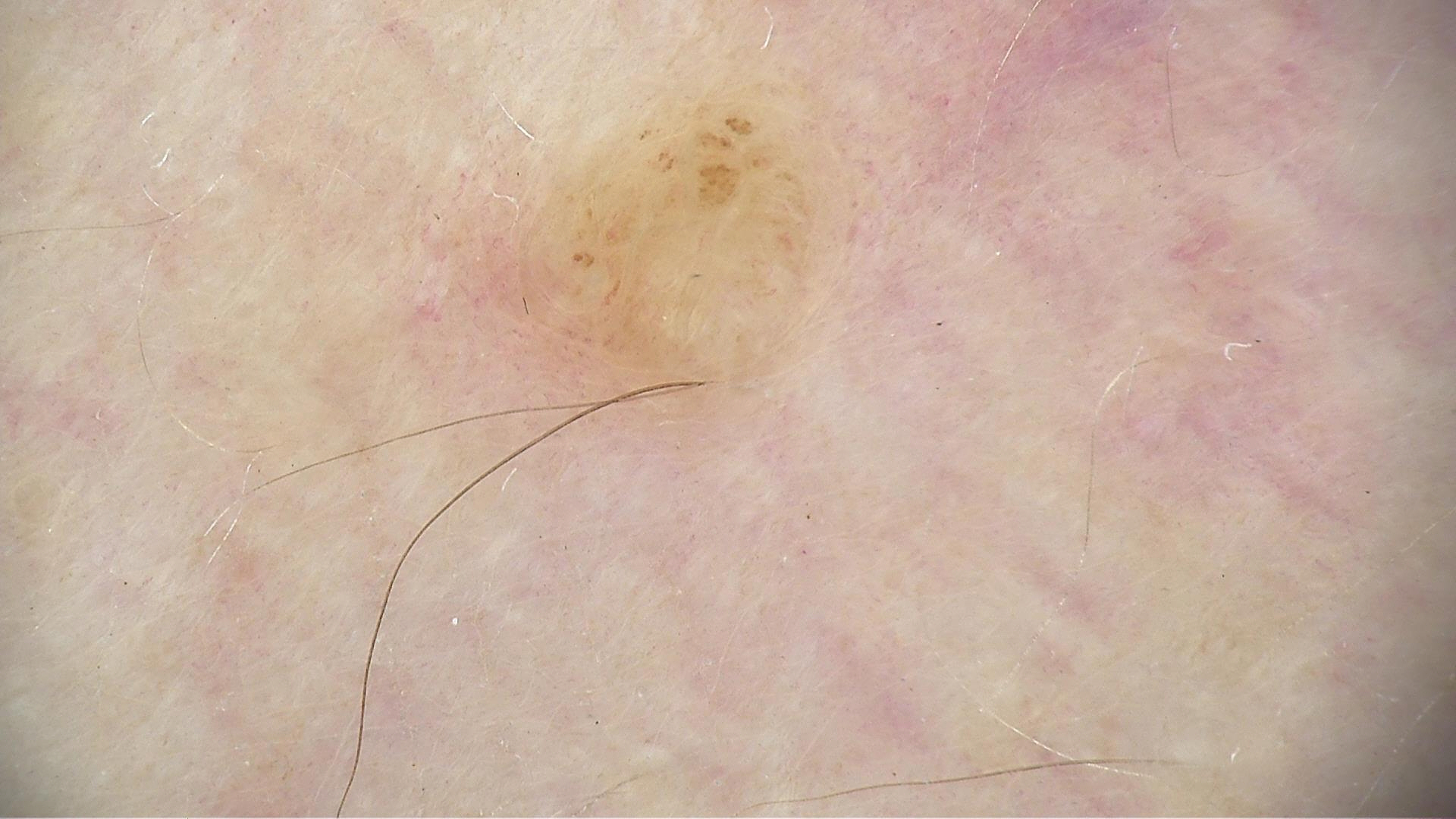  image: dermoscopy
  lesion_type:
    main_class: banal
    pattern: dermal
  diagnosis:
    name: dermal nevus
    code: db
    malignancy: benign
    super_class: melanocytic
    confirmation: expert consensus